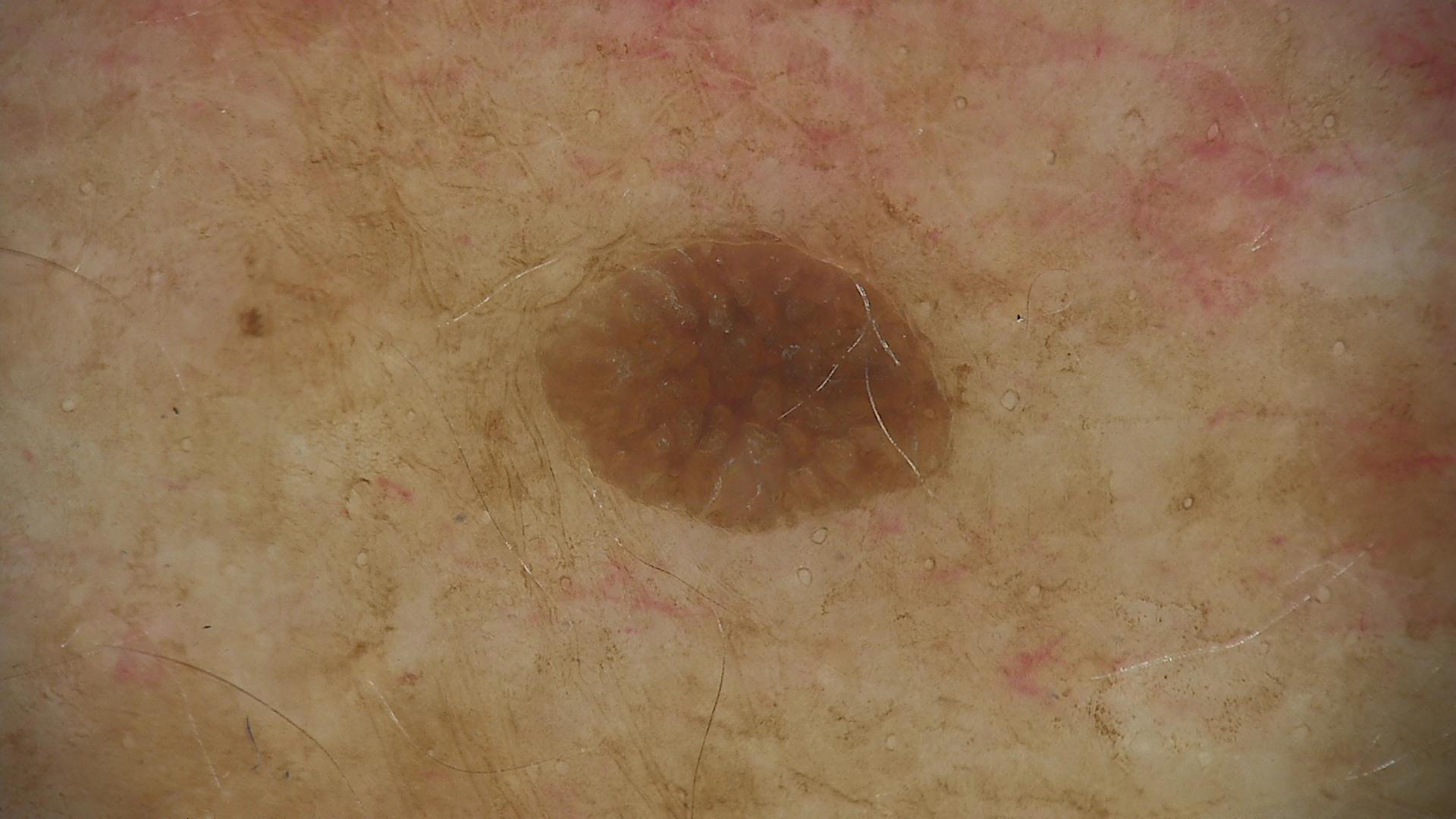A dermoscopic image of a skin lesion. Consistent with a keratinocytic lesion — a seborrheic keratosis.